A dermoscopic image of a skin lesion: 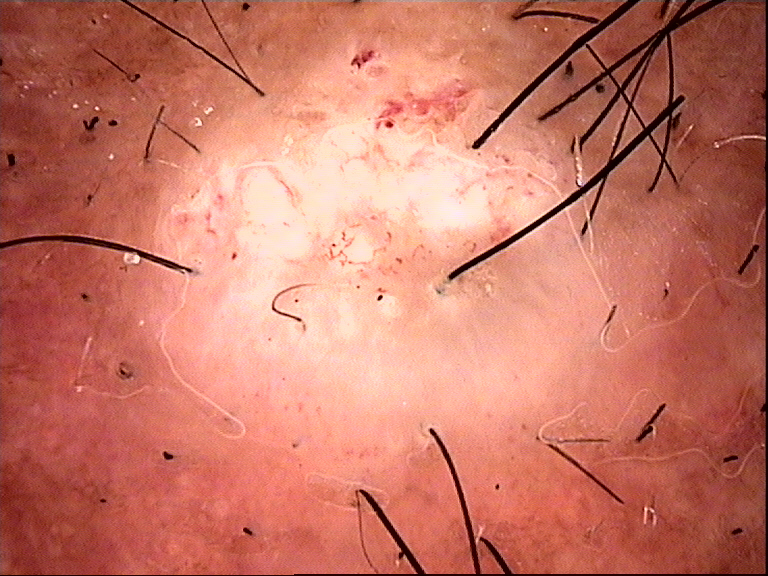Conclusion:
Biopsy-confirmed as a keratinocytic lesion — a squamous cell carcinoma.